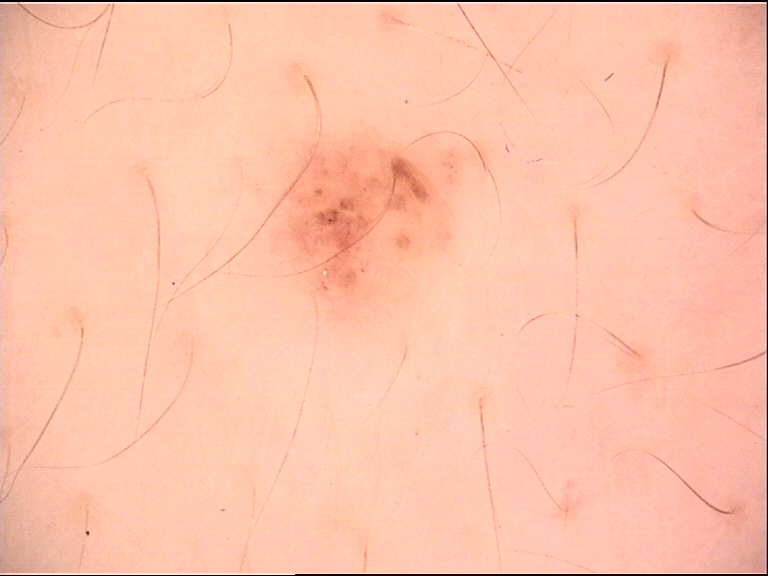Dermoscopy of a skin lesion. This is a banal lesion. Labeled as a compound nevus.